A female patient, roughly 20 years of age. This is a dermoscopic photograph of a skin lesion: 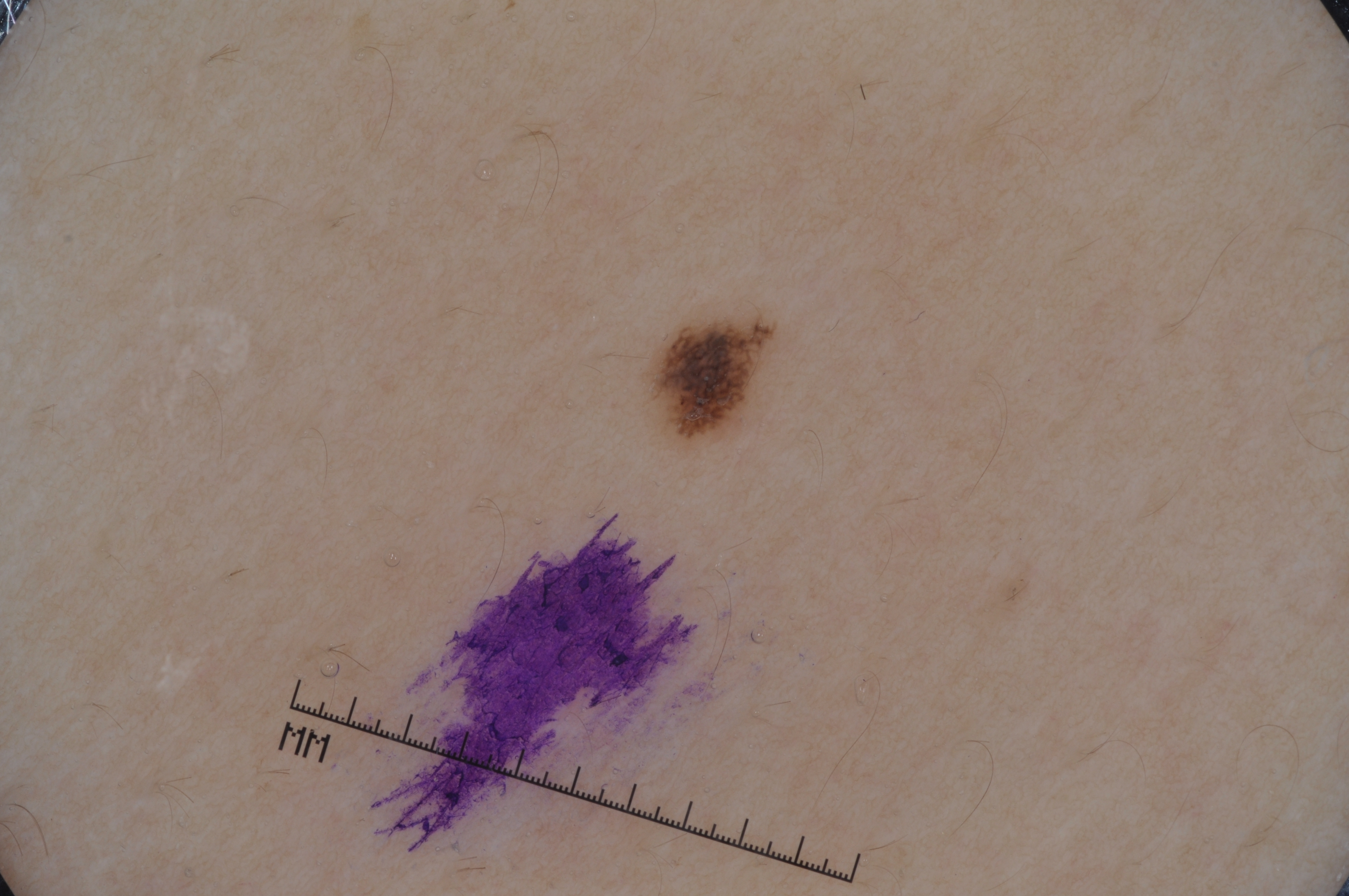Dermoscopic examination shows pigment network. The lesion's extent is left=639, top=303, right=779, bottom=445. A small lesion within a wider field of skin. Expert review diagnosed this as a melanocytic nevus, a benign skin lesion.